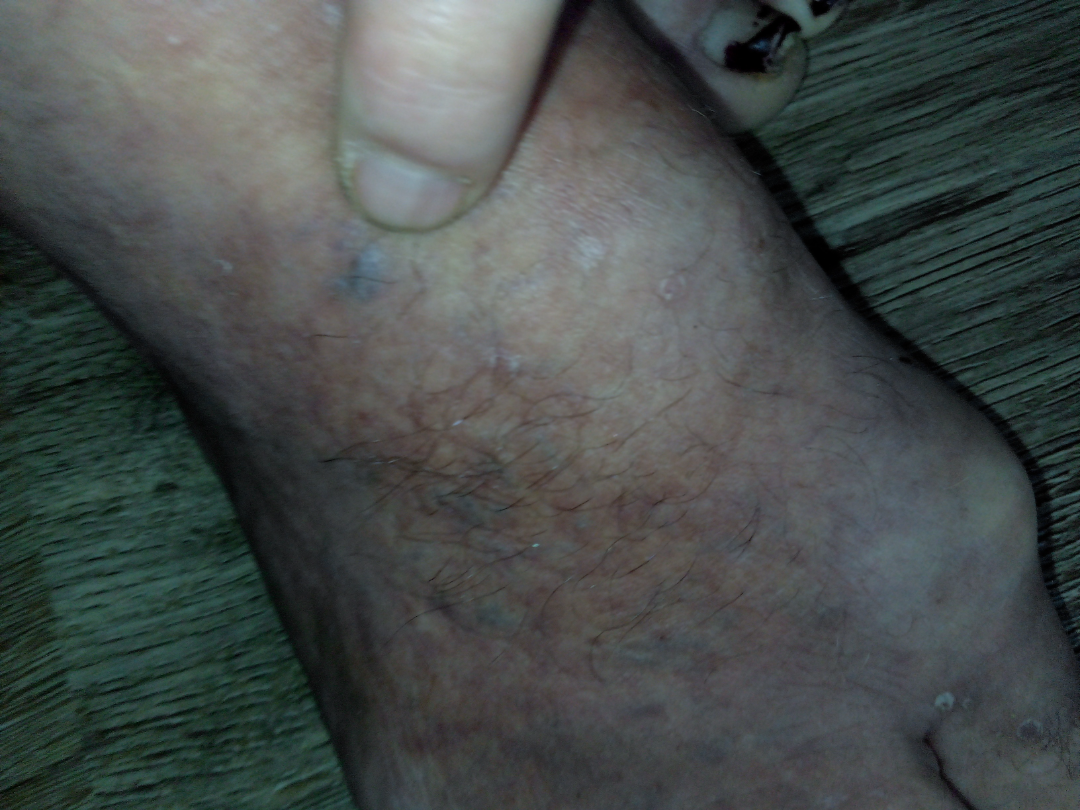The dermatologist could not determine a likely condition from the photograph alone.